A skin lesion imaged with a dermatoscope.
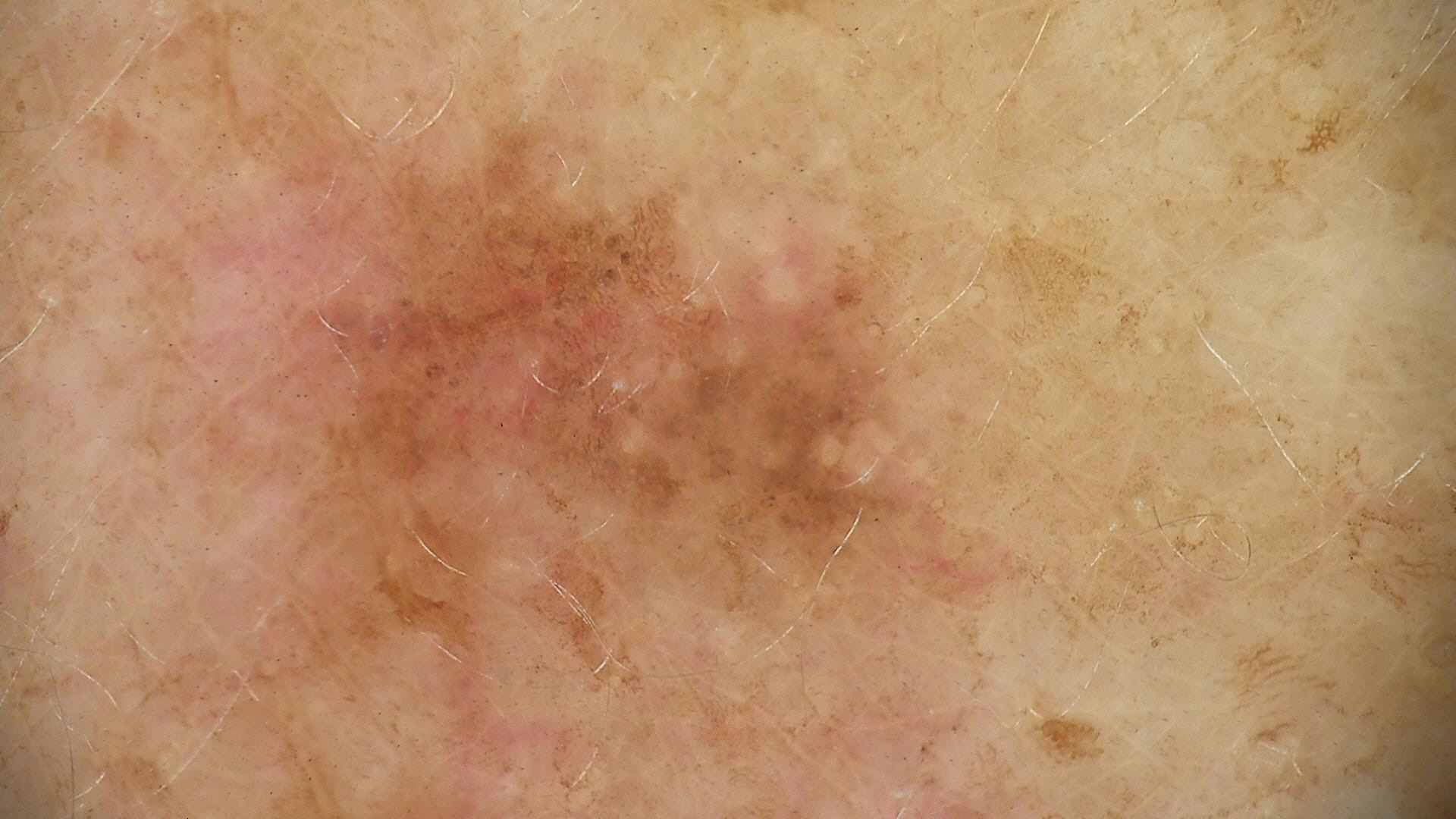The architecture is that of a keratinocytic lesion.
The diagnostic label was a benign lesion — a seborrheic keratosis.